Dermoscopy of a skin lesion: 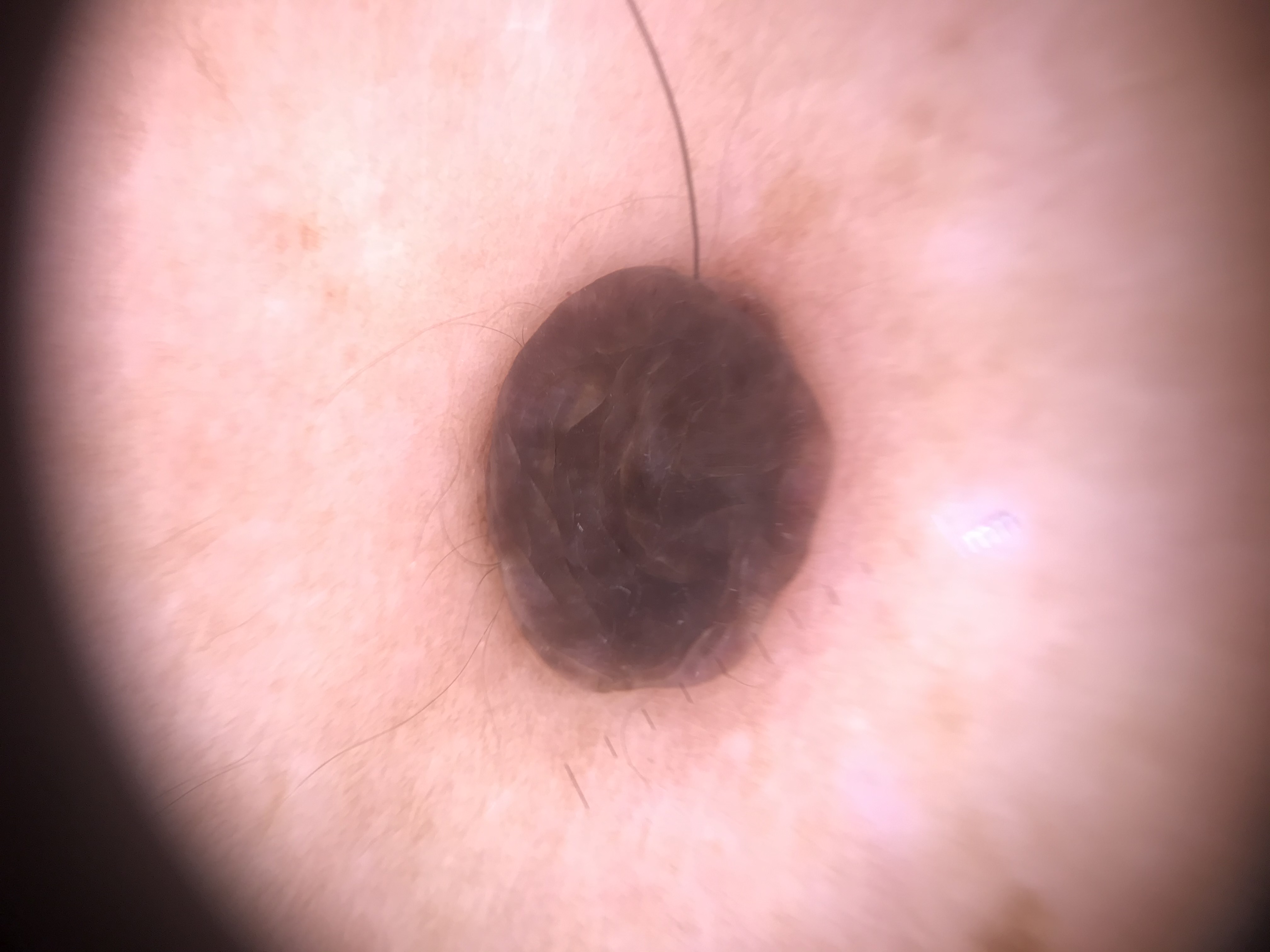This is a banal lesion.
Classified as a dermal nevus.